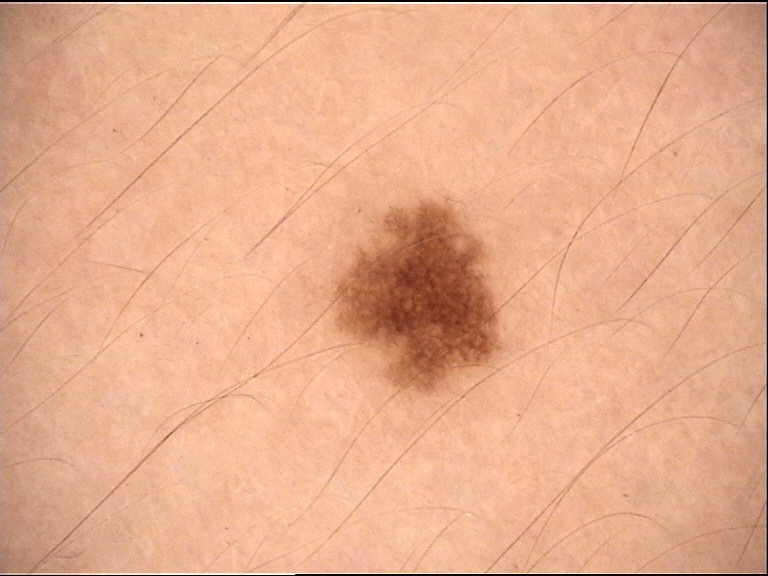{
  "diagnosis": {
    "name": "junctional nevus",
    "code": "jb",
    "malignancy": "benign",
    "super_class": "melanocytic",
    "confirmation": "expert consensus"
  }
}